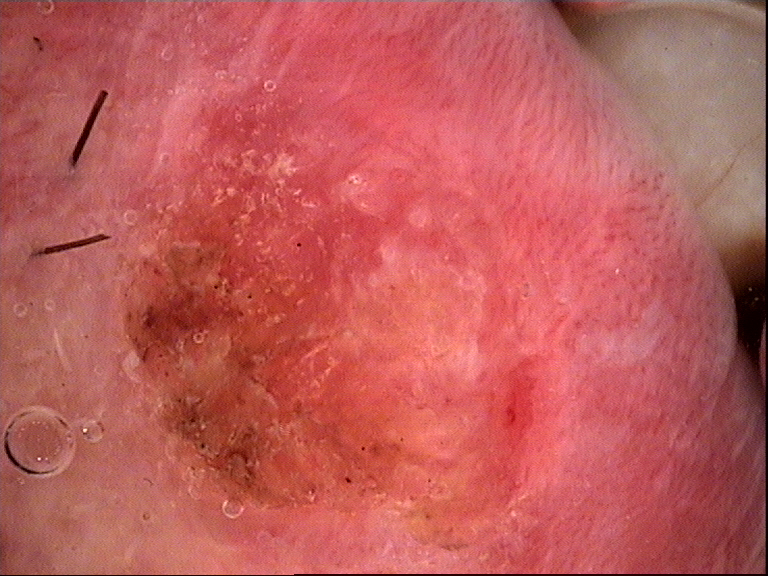pathology: squamous cell carcinoma (biopsy-proven).